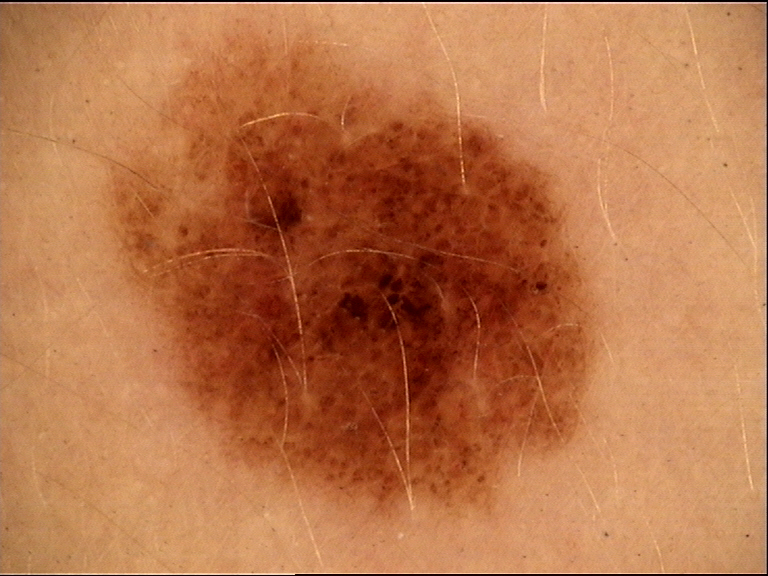Q: What is this lesion?
A: dysplastic junctional nevus (expert consensus)